The affected area is the palm. This image was taken at an angle. Texture is reported as raised or bumpy and fluid-filled. The patient described the issue as a rash — 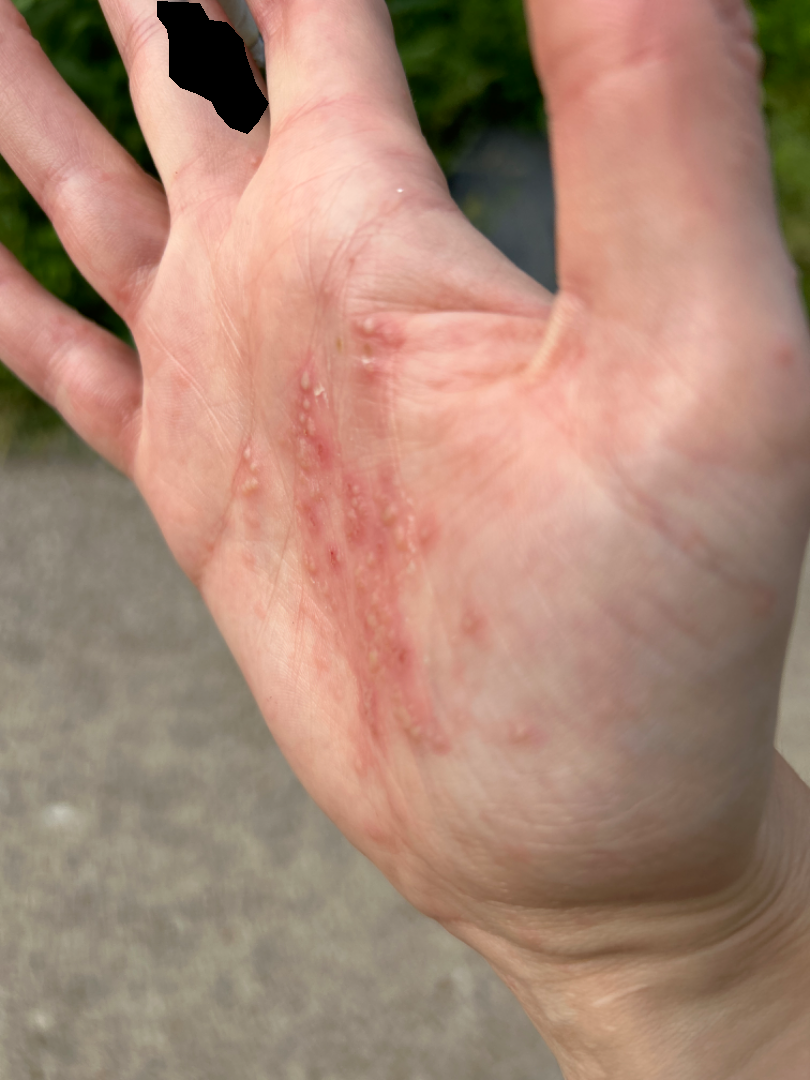  assessment: indeterminate